This is a dermoscopic photograph of a skin lesion. A female patient, aged around 60 — 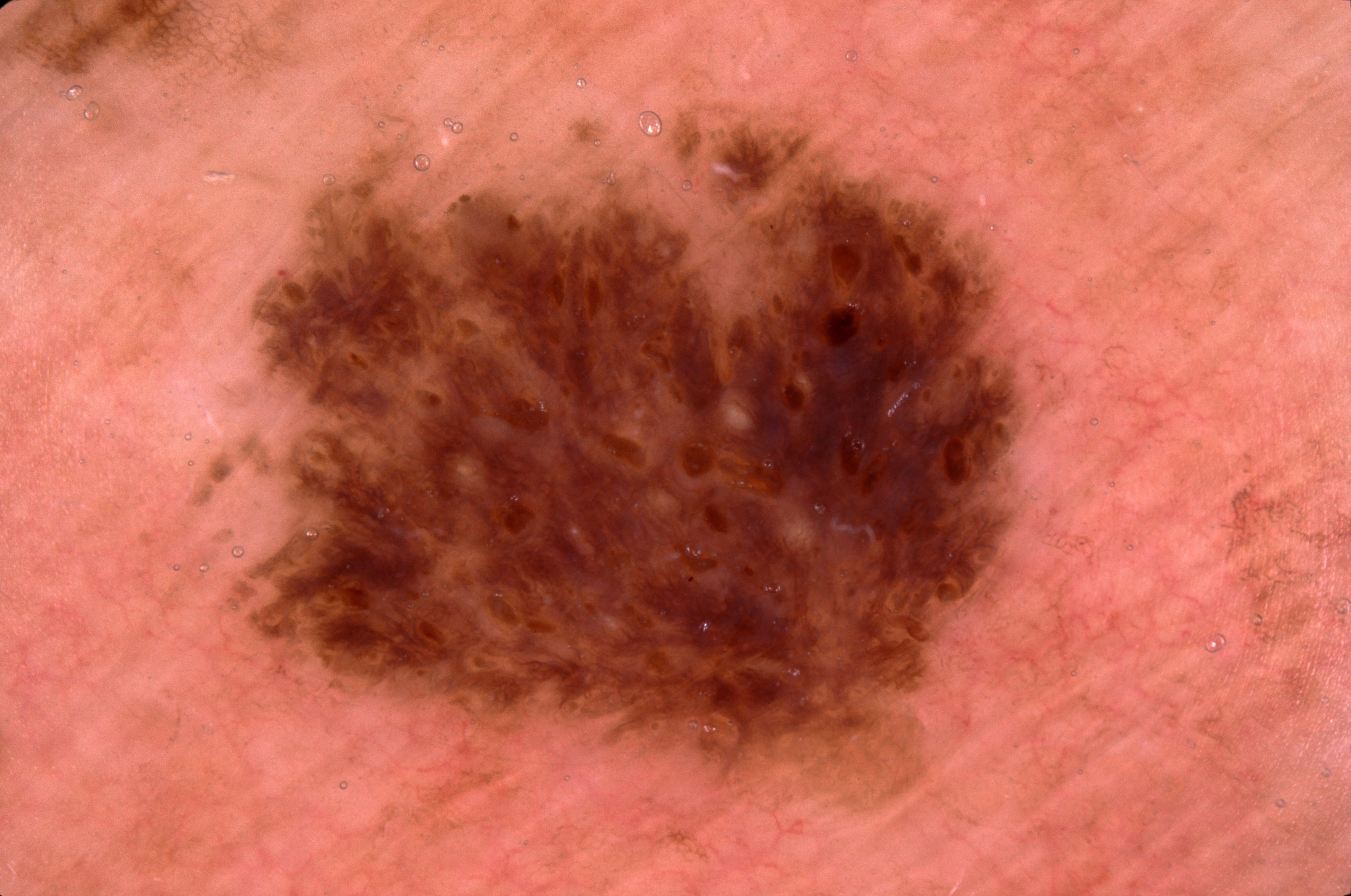As (left, top, right, bottom), the lesion's extent is [253, 126, 1024, 784]. Dermoscopic assessment notes milia-like cysts; no negative network, pigment network, or streaks. The diagnostic assessment was a seborrheic keratosis, a benign skin lesion.